A male patient, aged around 60; dermoscopy of a skin lesion: 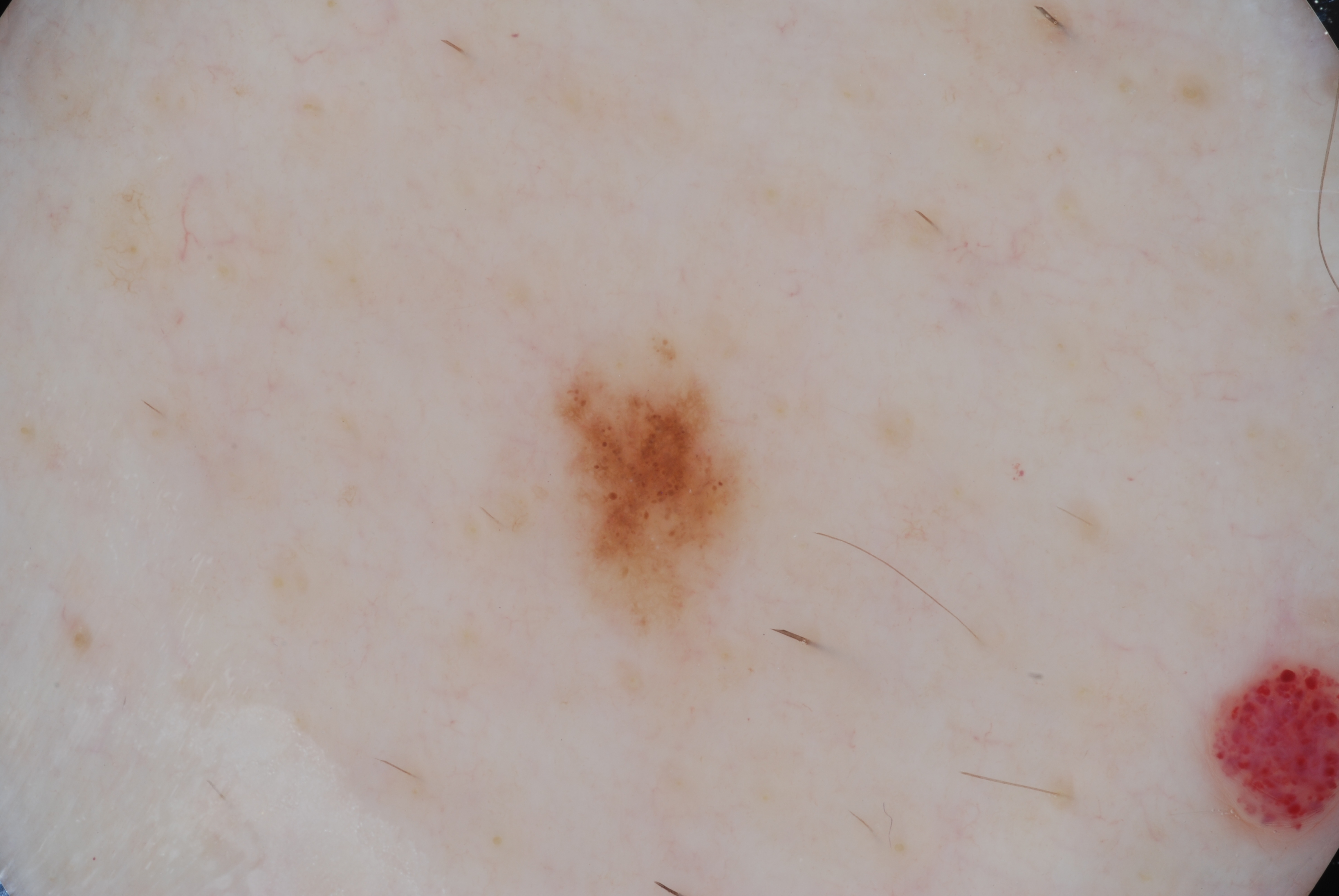Findings: On dermoscopy, the lesion shows milia-like cysts. With coordinates (x1, y1, x2, y2), the visible lesion spans bbox=[547, 332, 760, 663]. The lesion is small relative to the field of view. Impression: The lesion was assessed as a melanocytic nevus, a benign skin lesion.